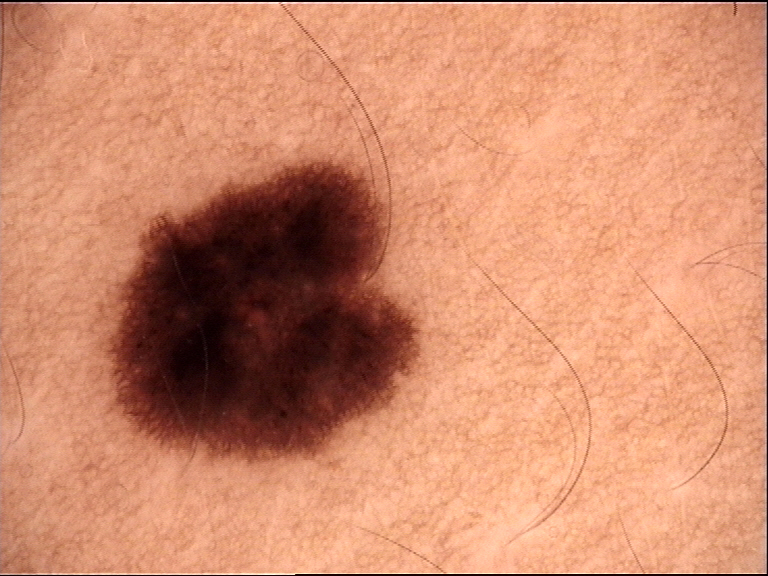class: junctional nevus (expert consensus).